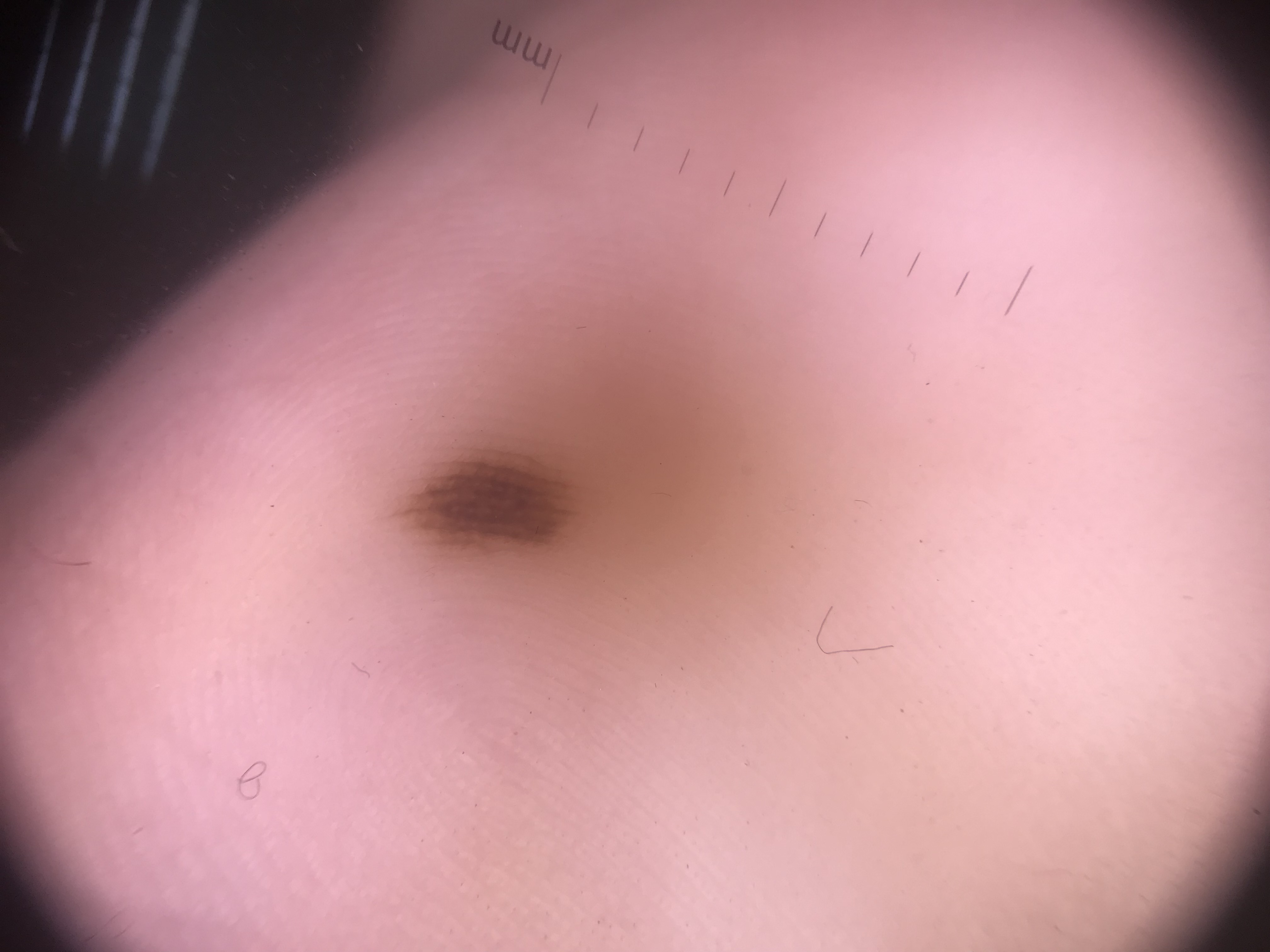A dermatoscopic image of a skin lesion.
The architecture is that of a banal lesion.
Labeled as an acral junctional nevus.